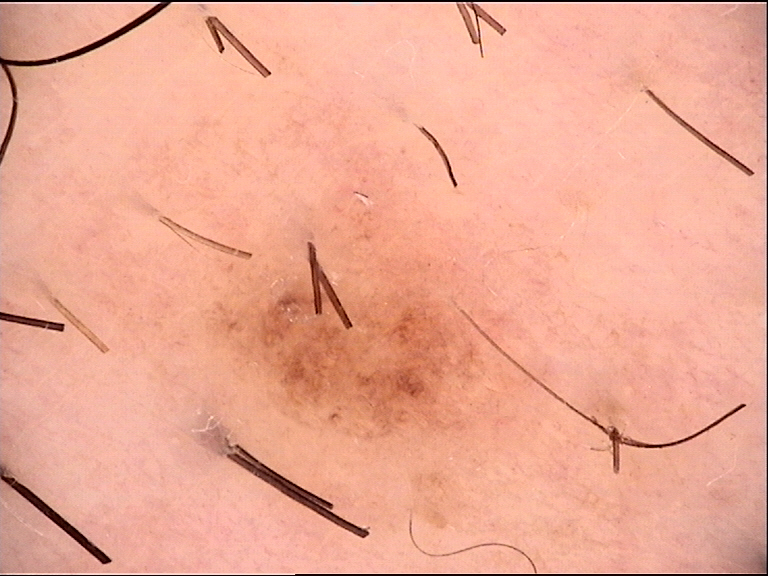class: dysplastic junctional nevus (expert consensus).